The patient considered this a rash. No relevant systemic symptoms. The patient indicates the condition has been present for less than one week. The lesion involves the head or neck and arm. Symptoms reported: bothersome appearance, burning, pain and itching. The photograph is a close-up of the affected area.
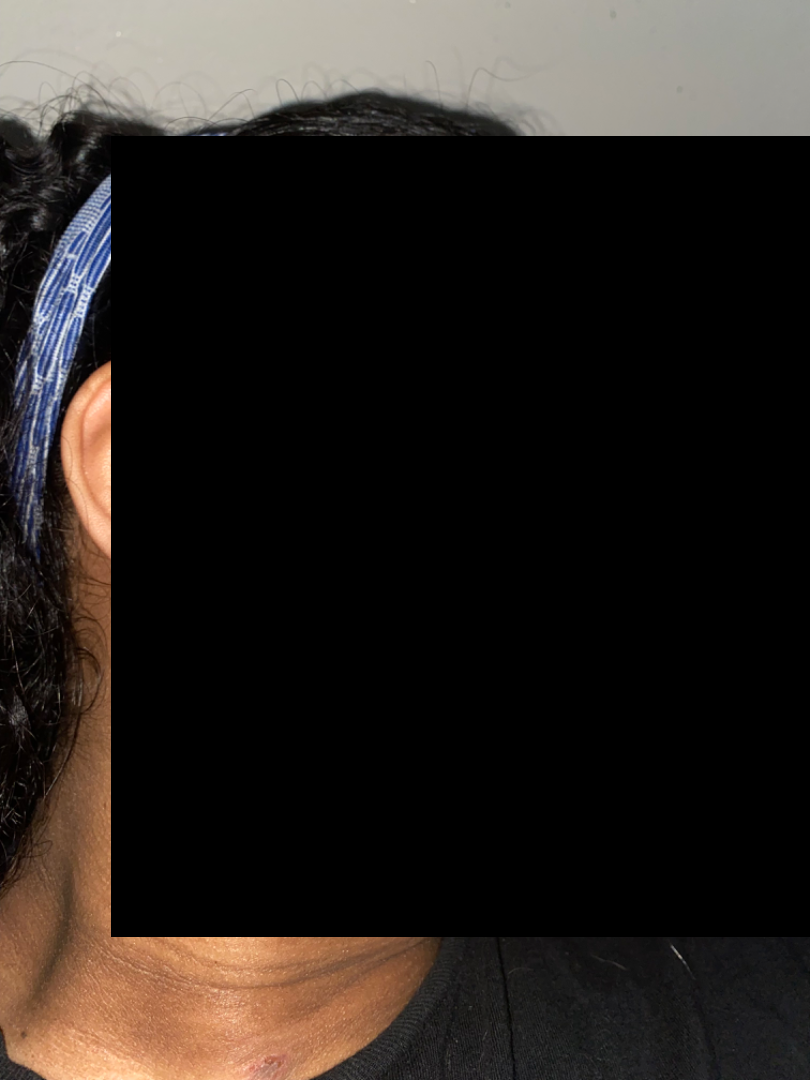| feature | finding |
|---|---|
| diagnostic considerations | the leading impression is Acne |